A dermatoscopic image of a skin lesion.
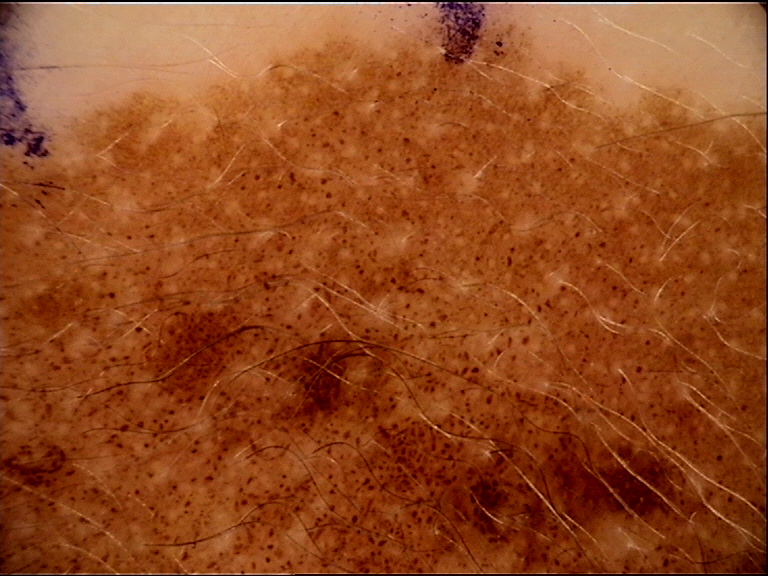Conclusion:
Labeled as a congenital junctional nevus.